A male subject 76 years of age; the patient describes having few moles overall; the patient says their skin reddens with sun exposure; on a questionnaire the patient reported a personal history of skin cancer and a personal history of cancer; imaged for a research study, with no referral diagnosis recorded: 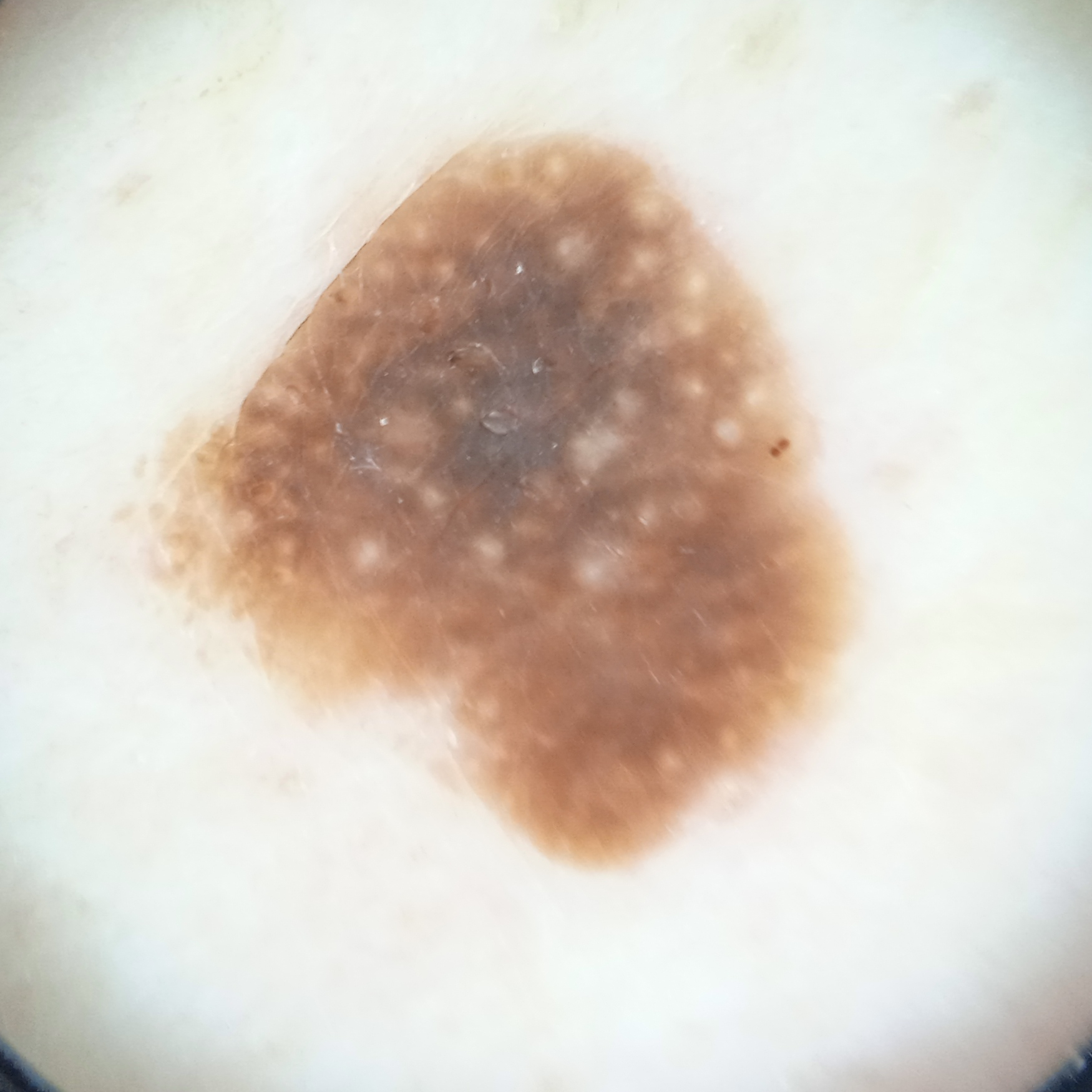Dermatologist review favored a seborrheic keratosis.